Self-categorized by the patient as a rash; texture is reported as rough or flaky, fluid-filled and raised or bumpy; the patient reports the condition has been present for one to three months; the subject is female; the photo was captured at an angle; reported lesion symptoms include itching: 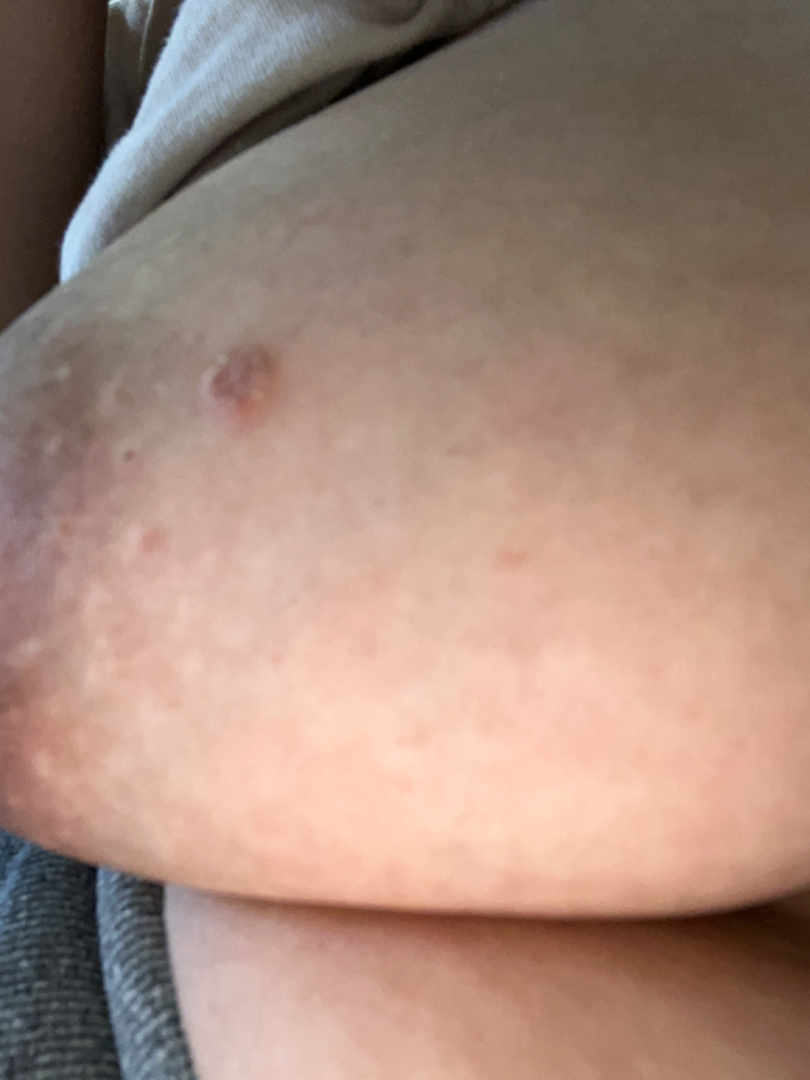Findings:
- impression: the differential is split between Eczema, Abscess and Impetigo